Dermoscopy of a skin lesion: 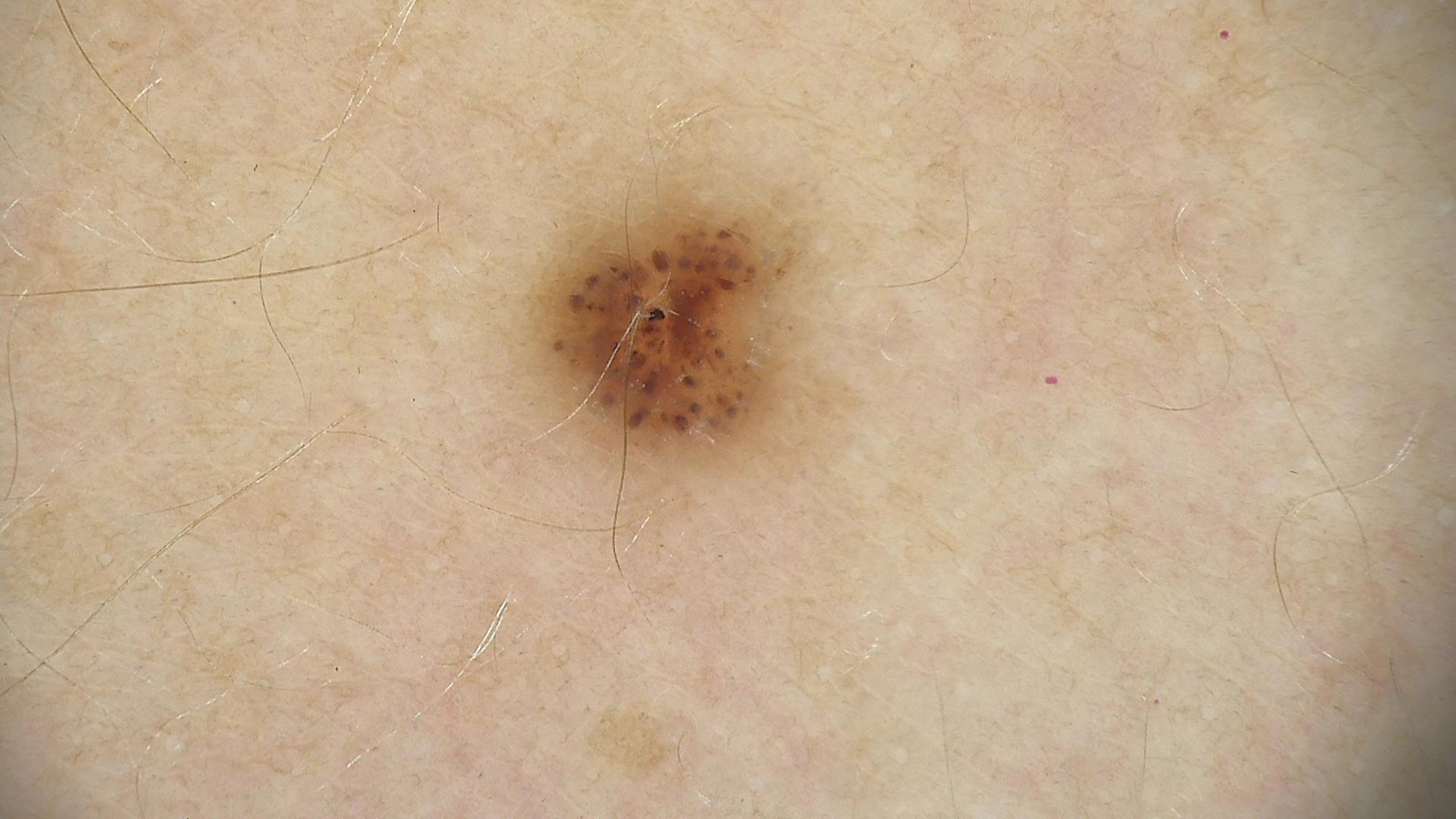Impression:
The diagnostic label was a benign lesion — a dysplastic junctional nevus.